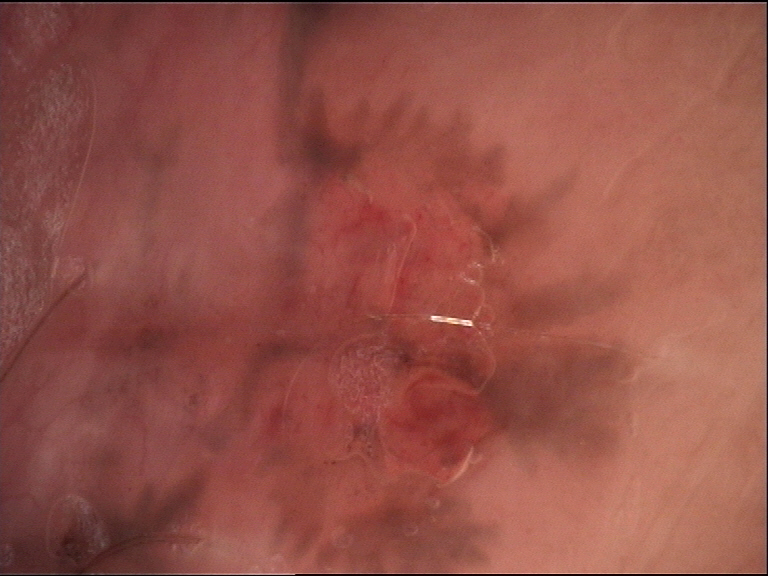Biopsy-confirmed as a basal cell carcinoma.